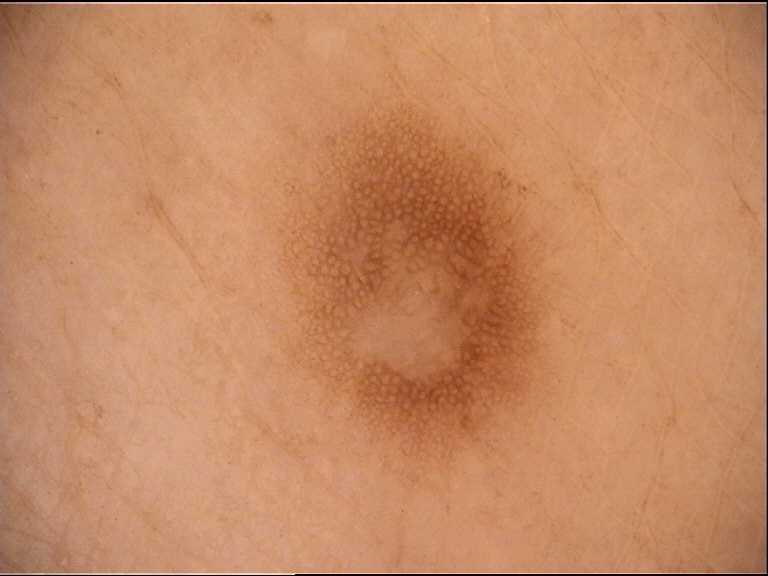A skin lesion imaged with a dermatoscope. The morphology is that of a fibro-histiocytic lesion. Classified as a dermatofibroma.